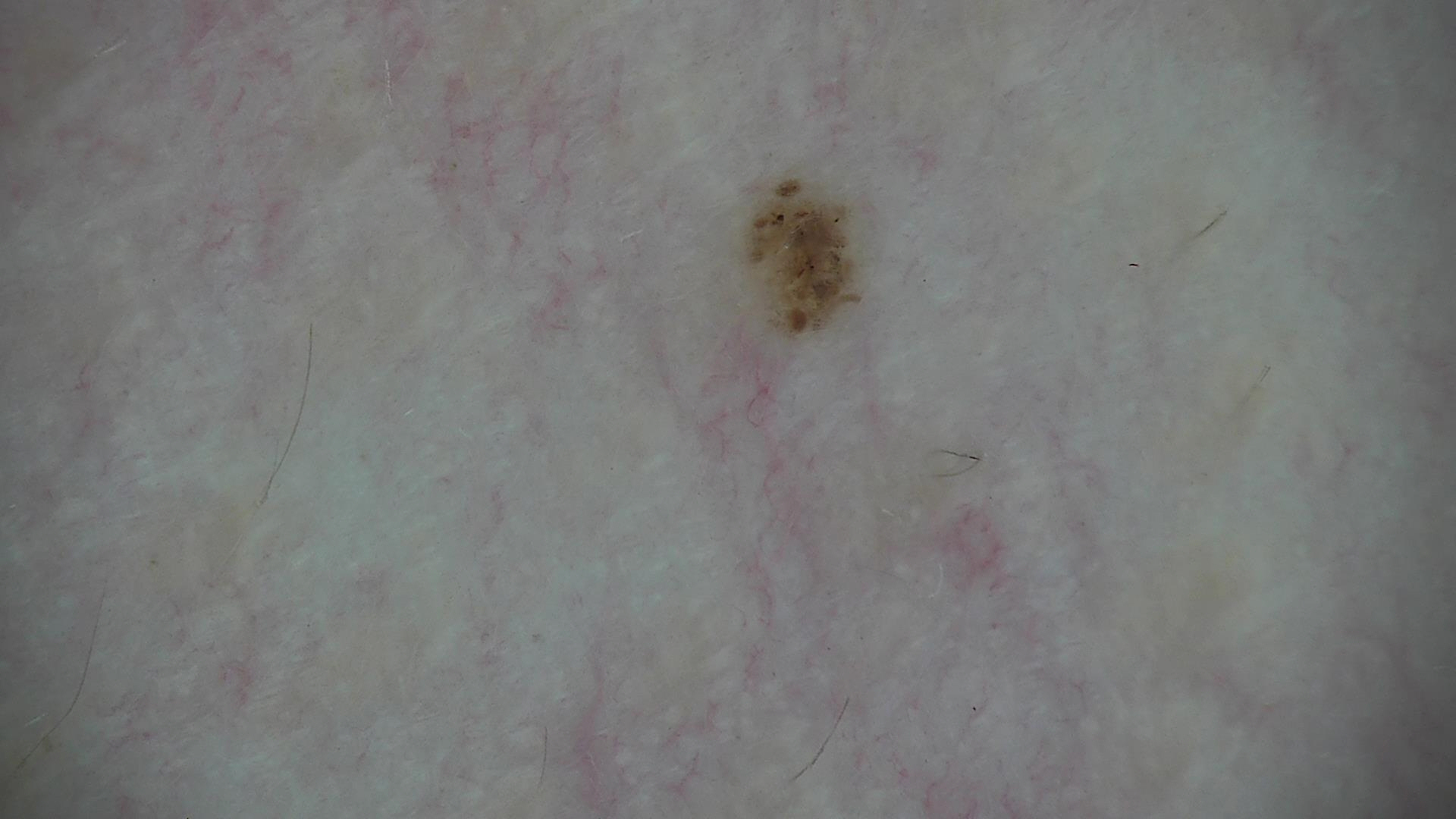Classified as a dysplastic junctional nevus.